Numerous moles by the patient's own estimate; acquired for a research image collection, with no referral diagnosis; a skin lesion imaged with a dermatoscope: 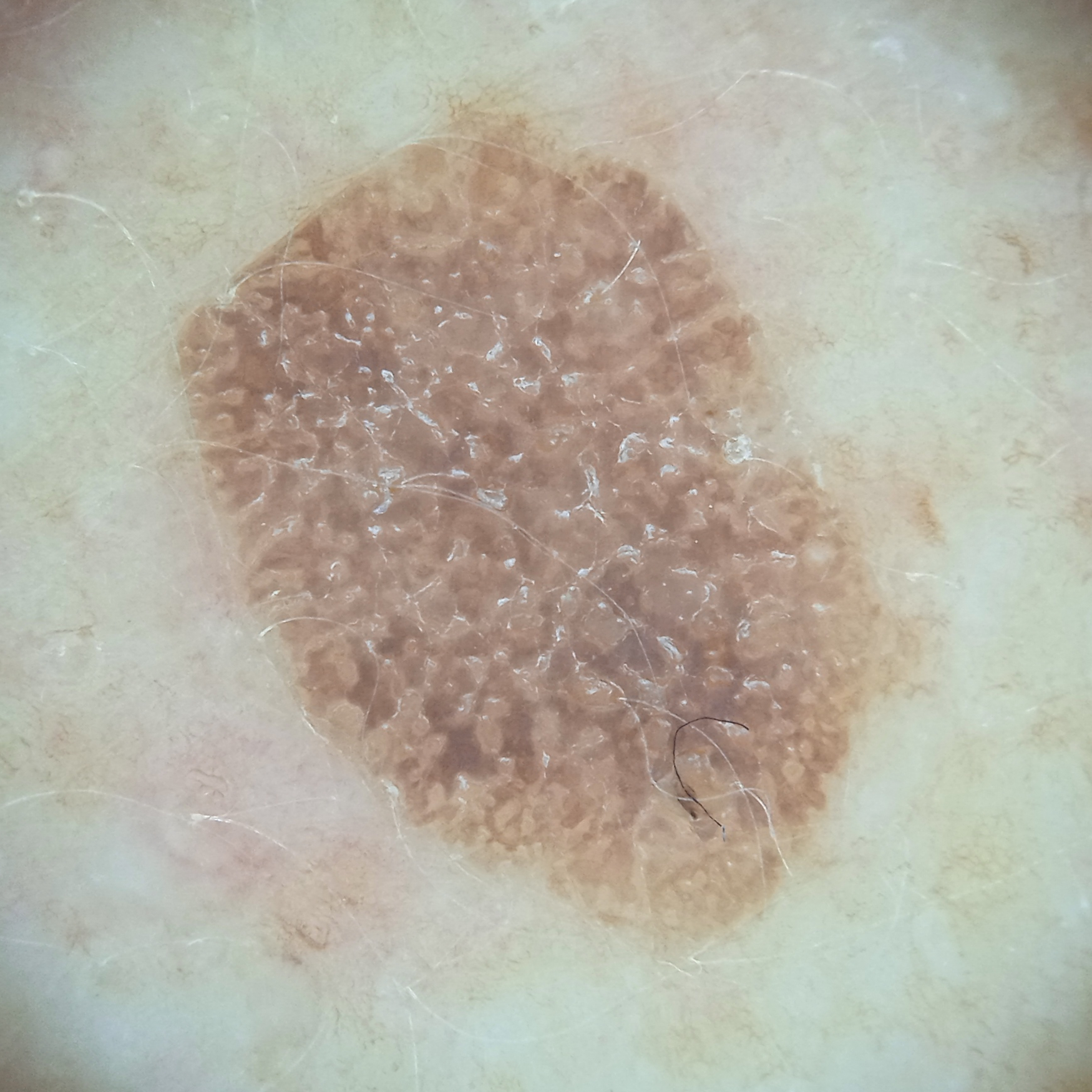| field | value |
|---|---|
| diameter | 9.6 mm |
| diagnostic label | seborrheic keratosis (dermatologist consensus) |